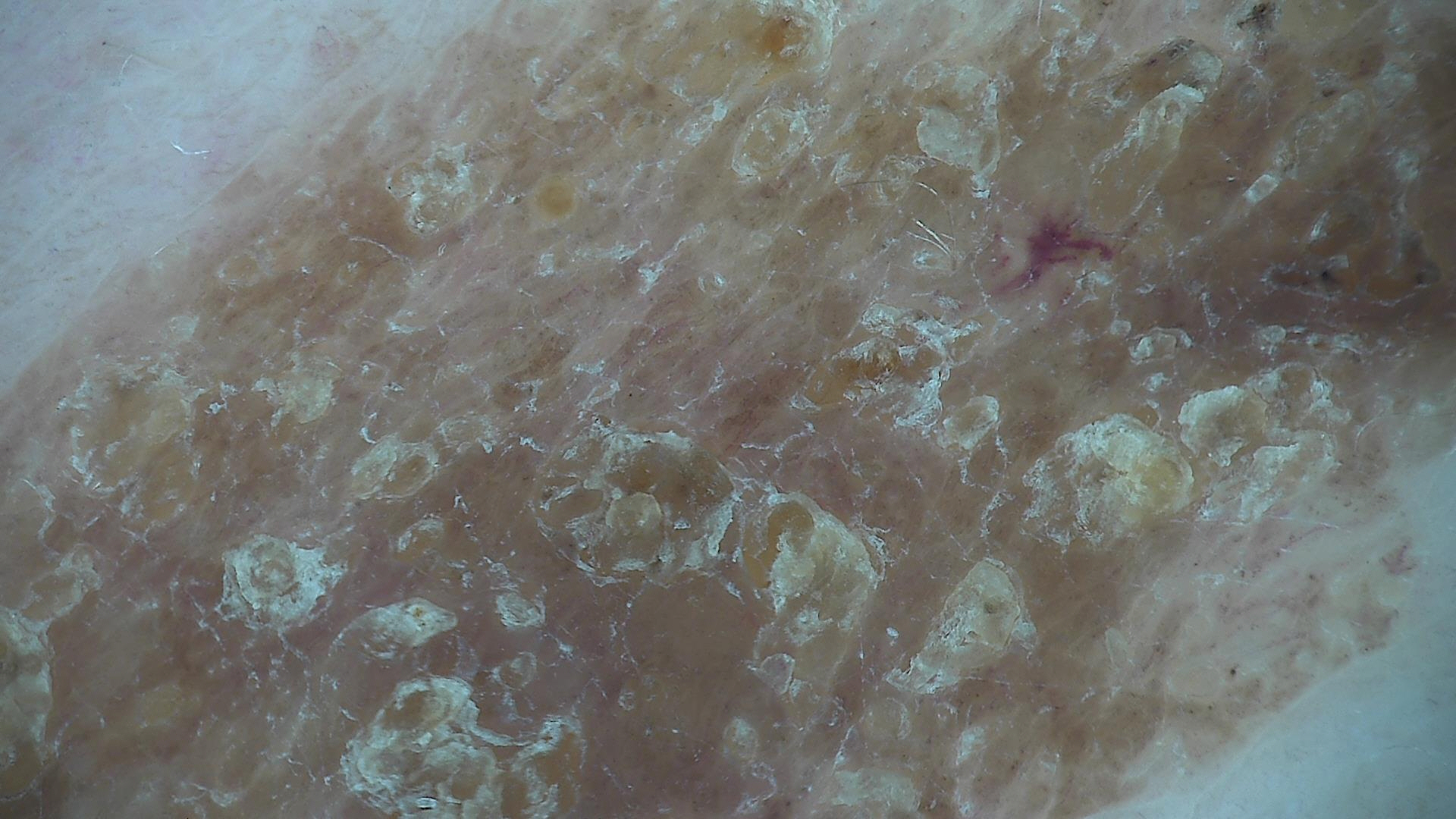subtype = keratinocytic
label = seborrheic keratosis (expert consensus)